A dermoscopy image of a single skin lesion.
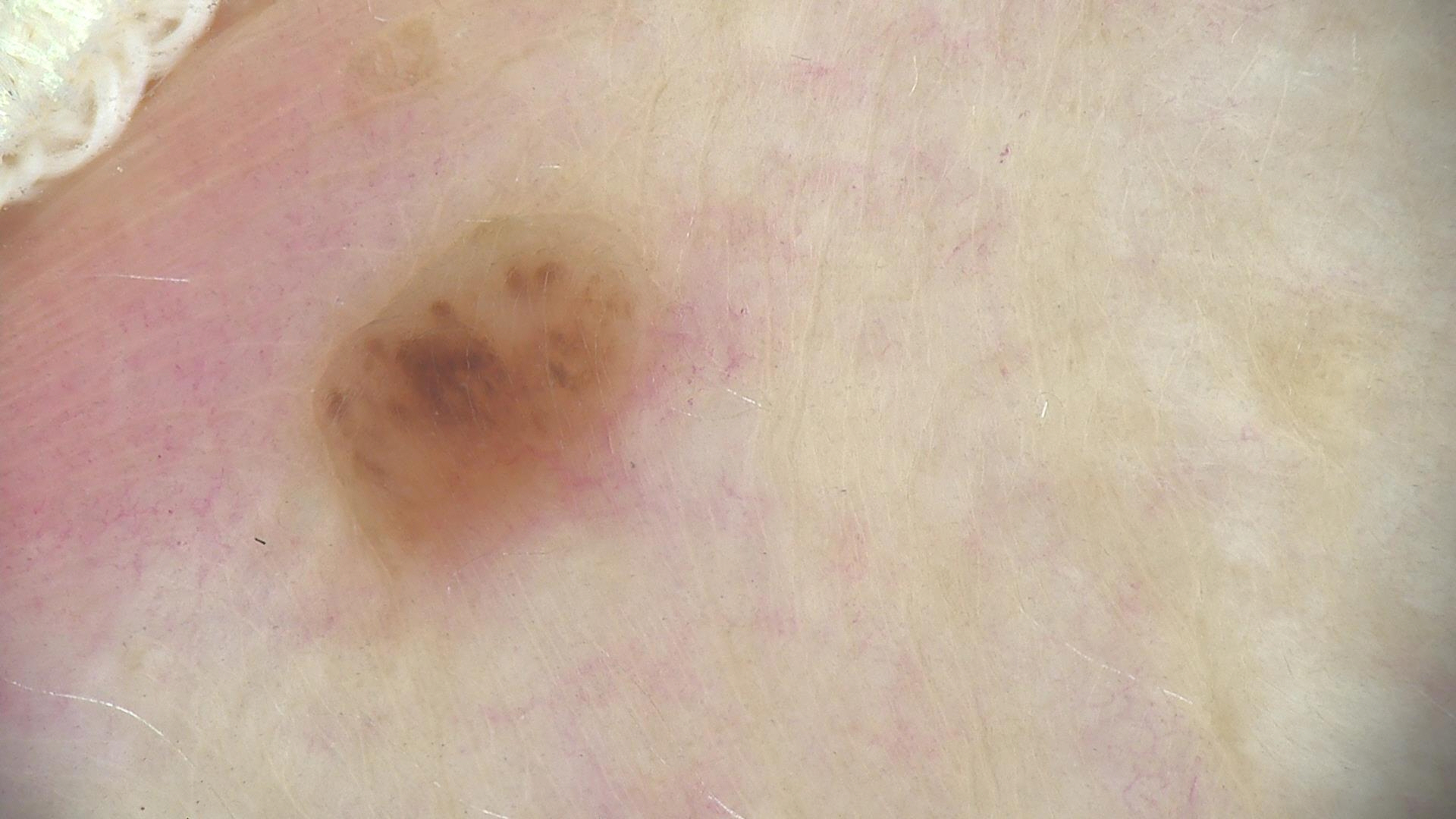Case:
The morphology is that of a banal lesion.
Impression:
Diagnosed as a dermal nevus.